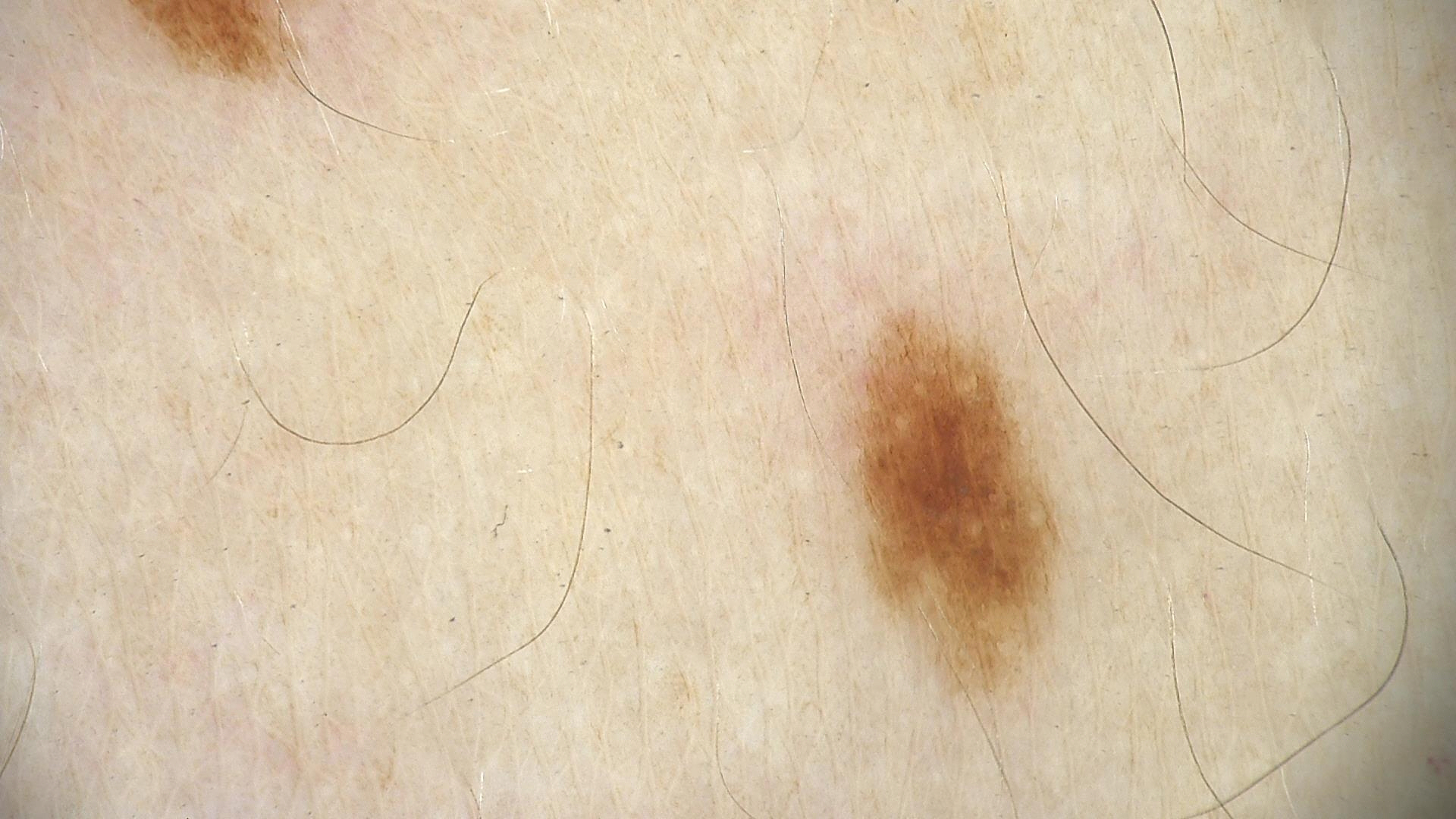diagnosis:
  name: junctional nevus
  code: jb
  malignancy: benign
  super_class: melanocytic
  confirmation: expert consensus